The chart notes a first-degree relative with melanoma but no previous melanoma; a male subject aged 38 to 42; the patient is Fitzpatrick skin type III; a dermatoscopic image of a skin lesion — 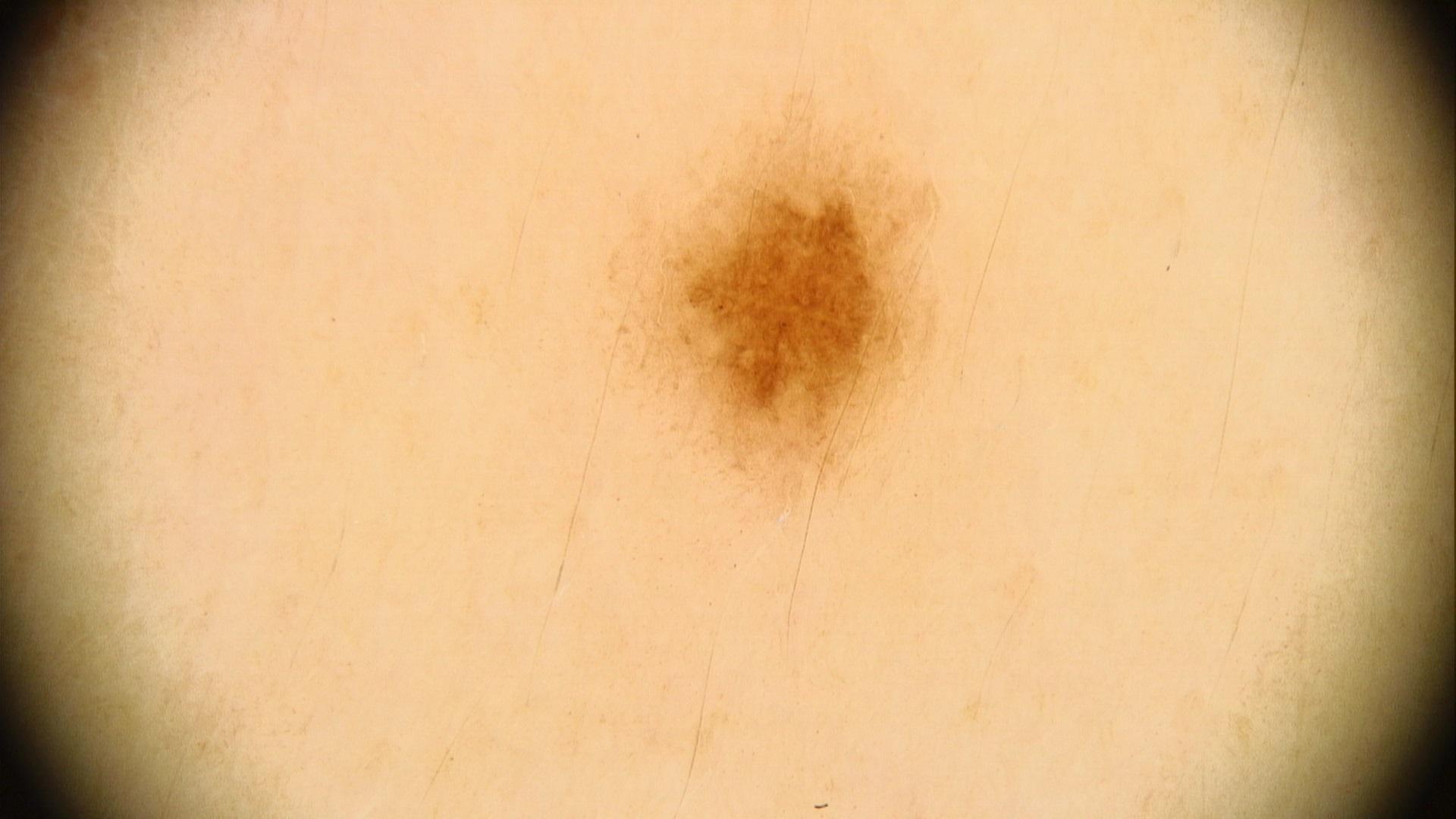Q: What is the diagnosis?
A: Nevus (clinical impression)